Present for about one day · the lesion is described as raised or bumpy · the patient notes itching · the subject is a male aged 18–29 · this is a close-up image · the patient considered this a rash.
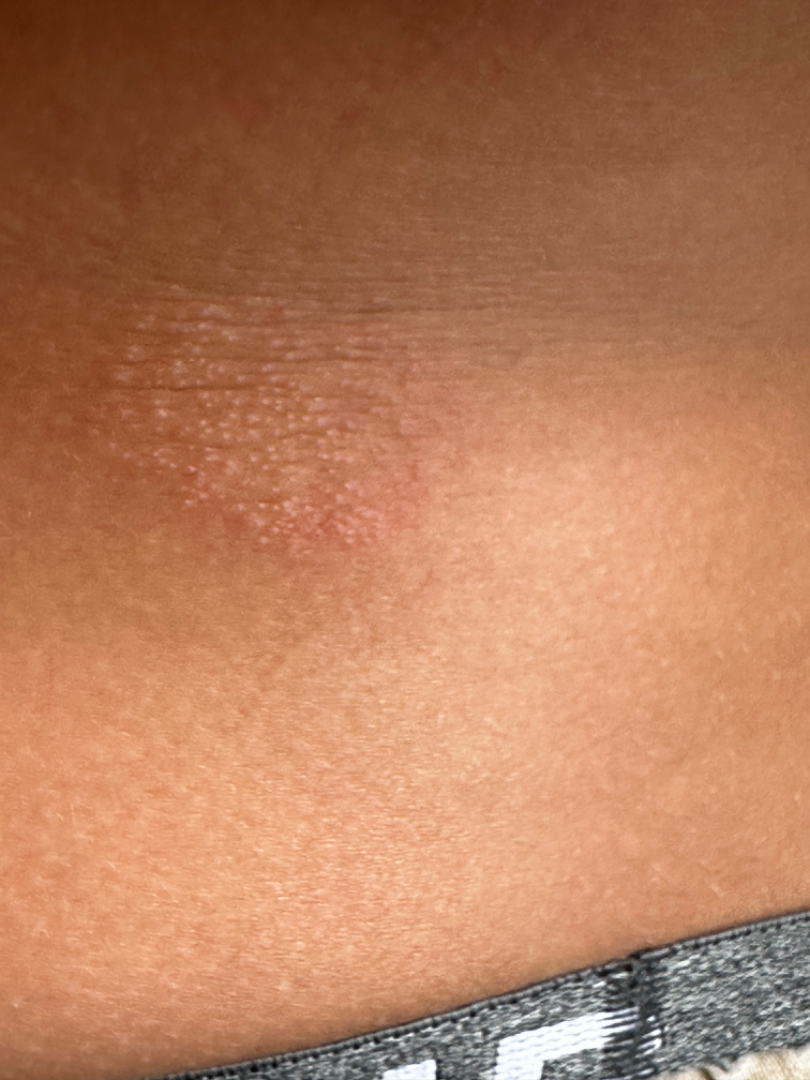<summary>
<differential>
  <leading>Eczema</leading>
  <considered>Lichen nitidus</considered>
</differential>
</summary>